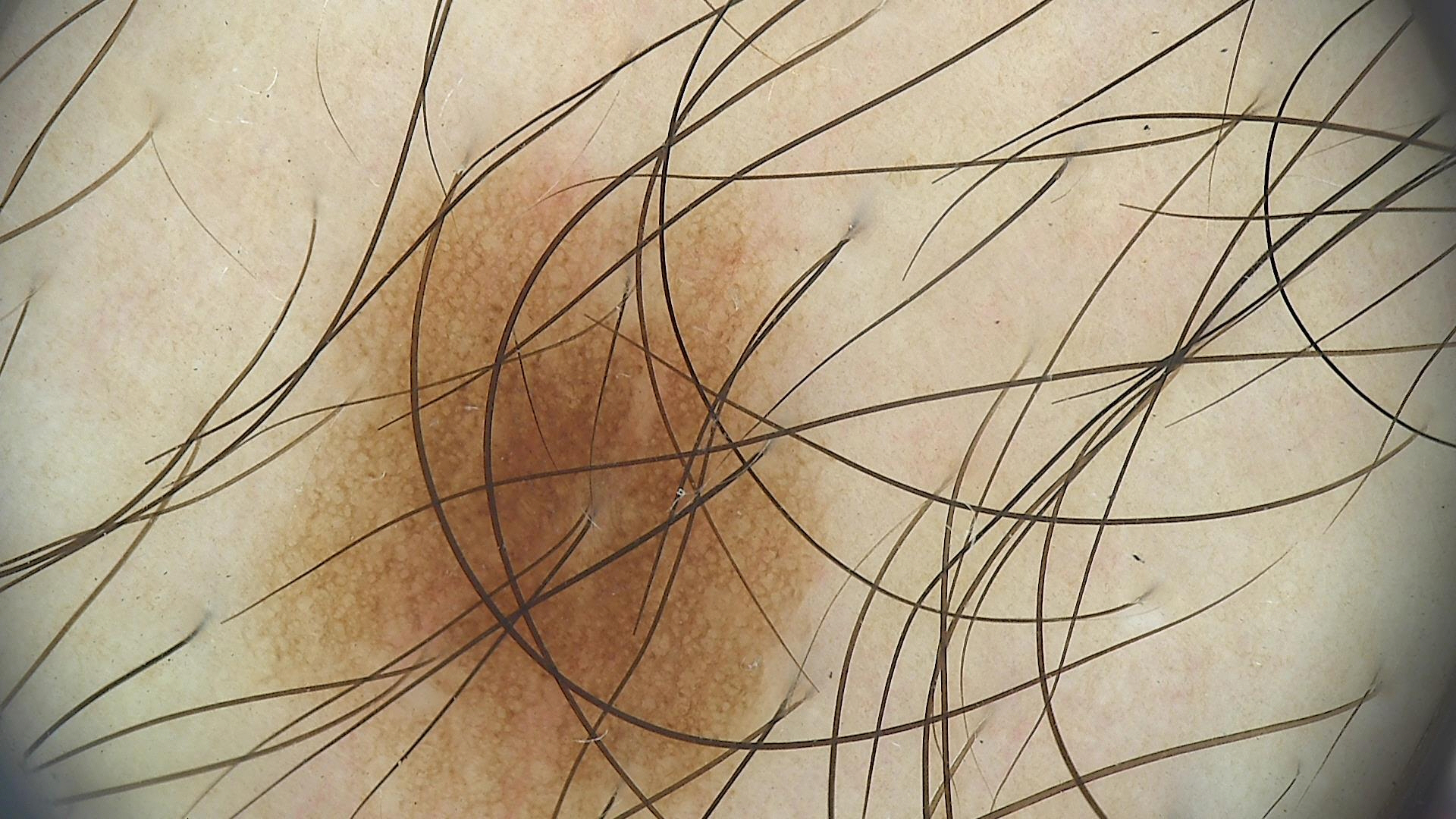The diagnosis was a benign lesion — a dysplastic junctional nevus.